A dermoscopic close-up of a skin lesion.
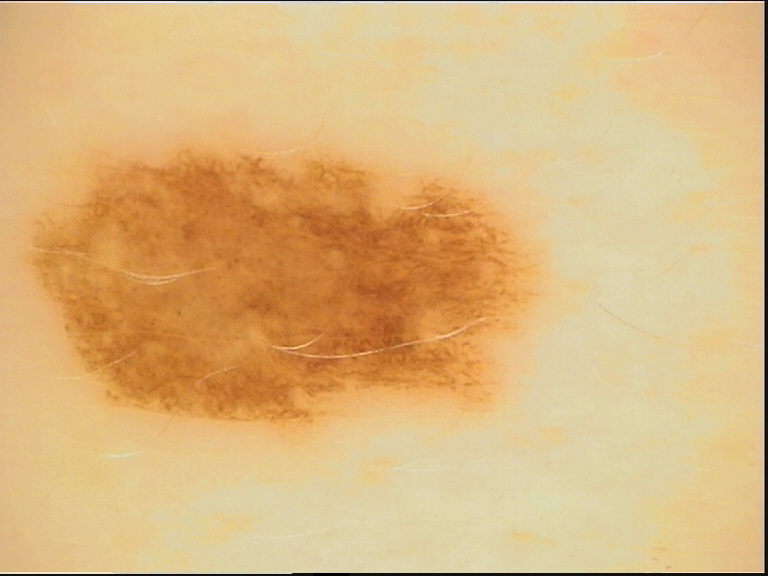Impression: The diagnostic label was a benign lesion — a dysplastic junctional nevus.